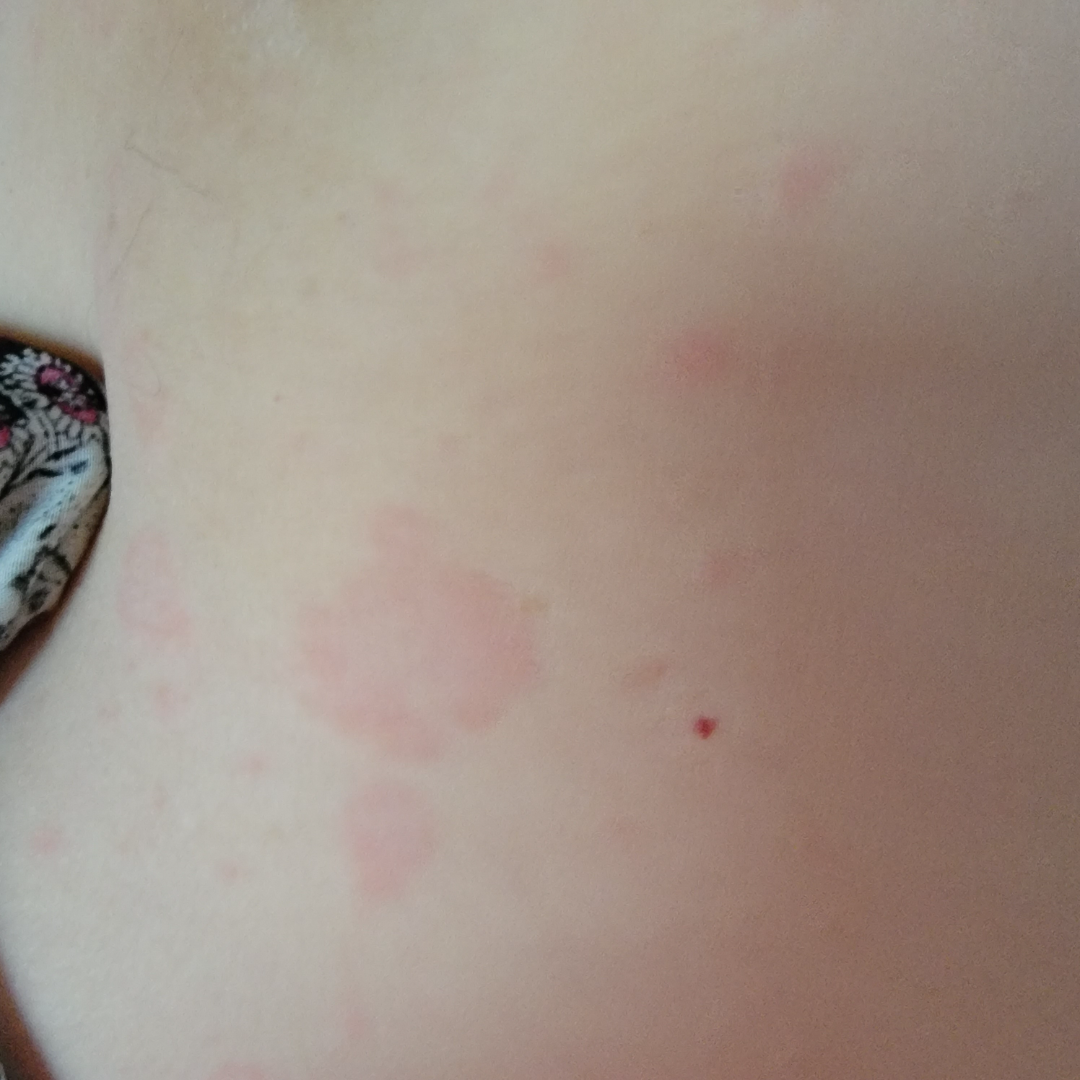The case was indeterminate on photographic review.